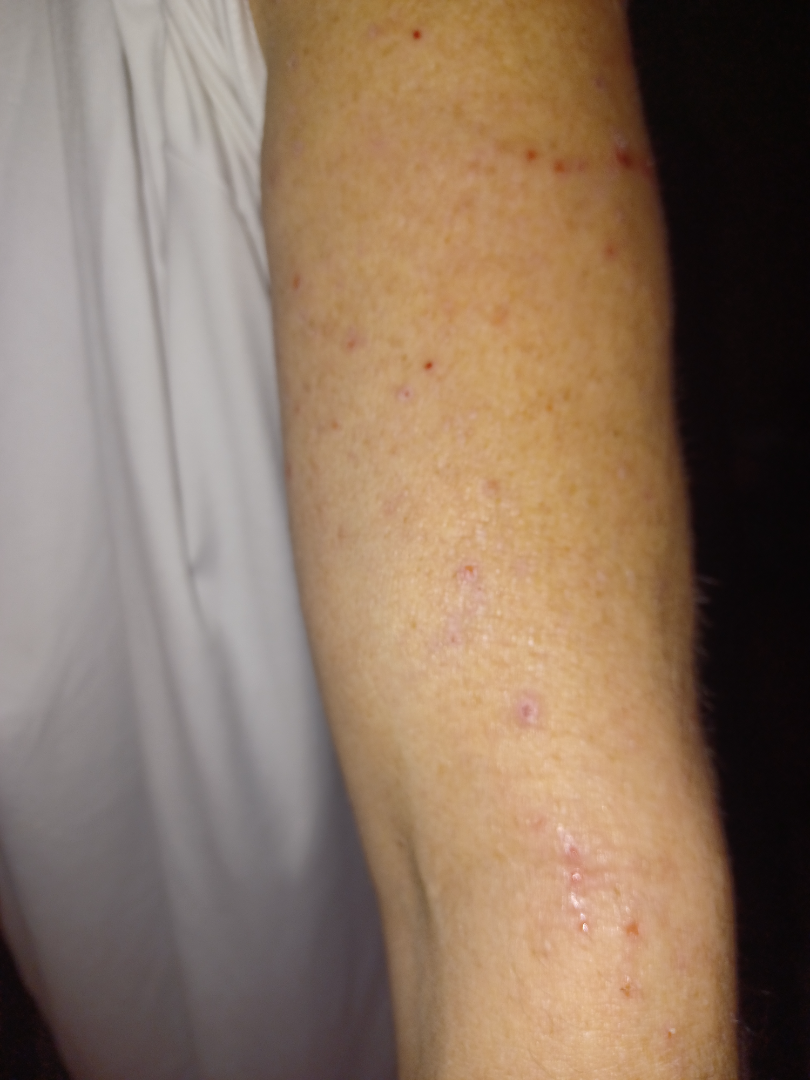The reviewing dermatologist was unable to assign a differential diagnosis from the image. This image was taken at a distance.